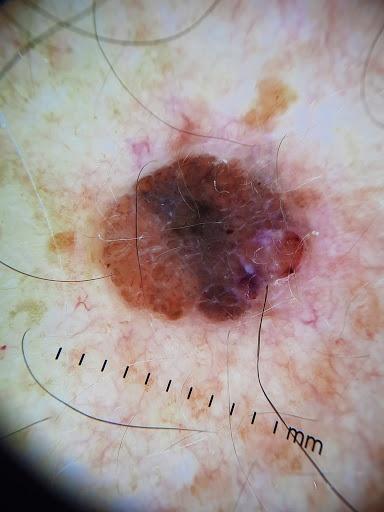A male patient roughly 65 years of age. A dermoscopy image of a single skin lesion. The lesion is on the trunk, specifically the posterior trunk. Histopathology confirmed a melanoma.